The chart notes no melanoma in first-degree relatives and no previous melanoma · a female patient in their mid-50s · Fitzpatrick skin type IV · a contact-polarized dermoscopy image of a skin lesion.
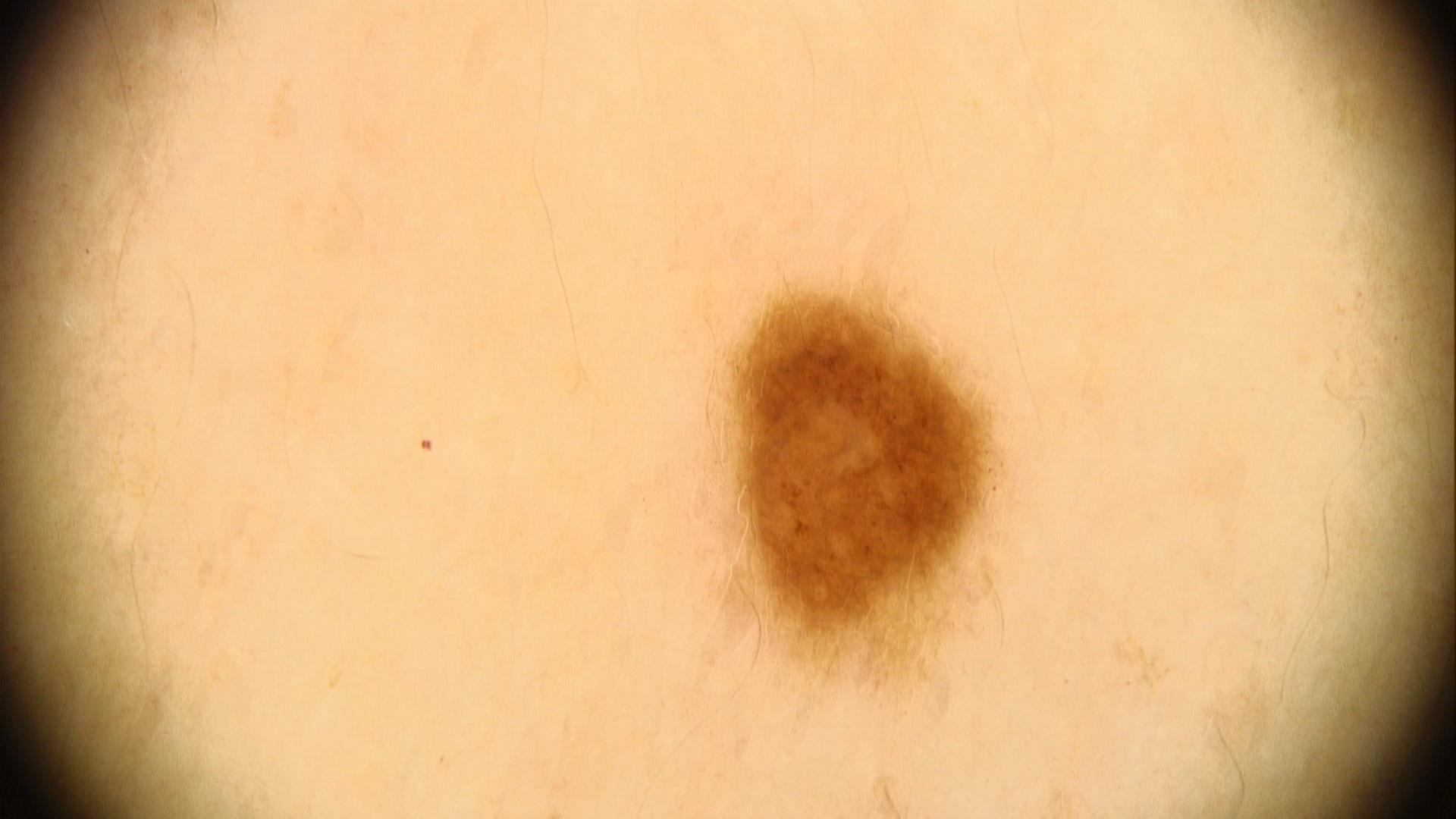Findings:
The lesion is on the trunk, specifically the posterior trunk.
Assessment:
The clinical impression was a nevus.